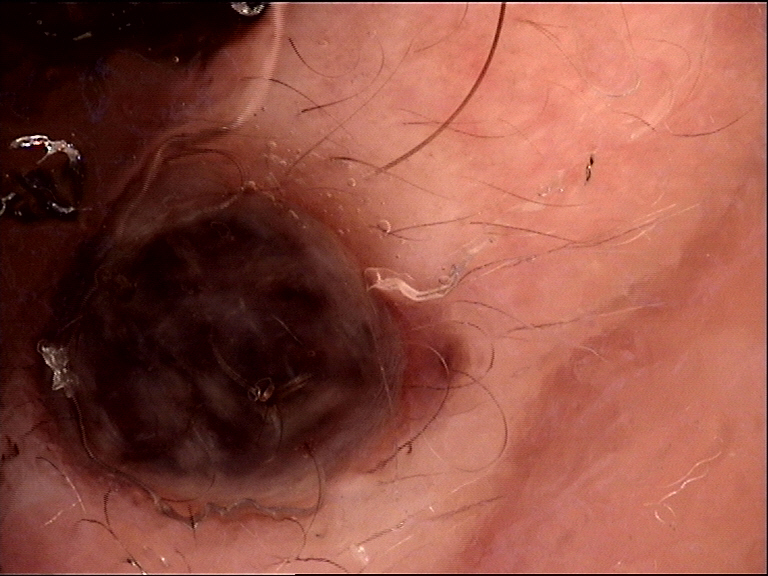The diagnosis was a dermal nevus.